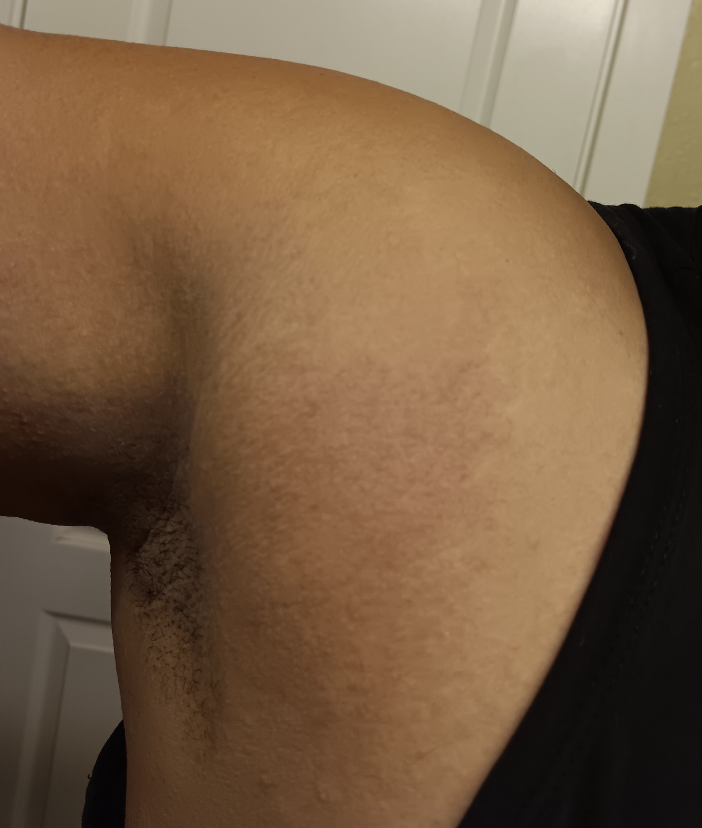assessment = ungradable on photographic review; reported symptoms = burning and itching; texture = raised or bumpy; photo taken = at a distance; duration = one to four weeks; affected area = leg, head or neck and arm; self-categorized as = acne.